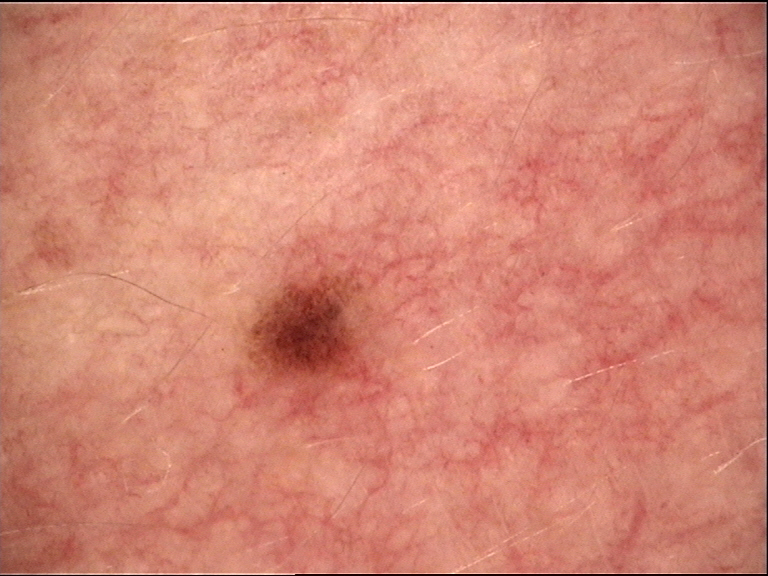Diagnosed as a dysplastic junctional nevus.